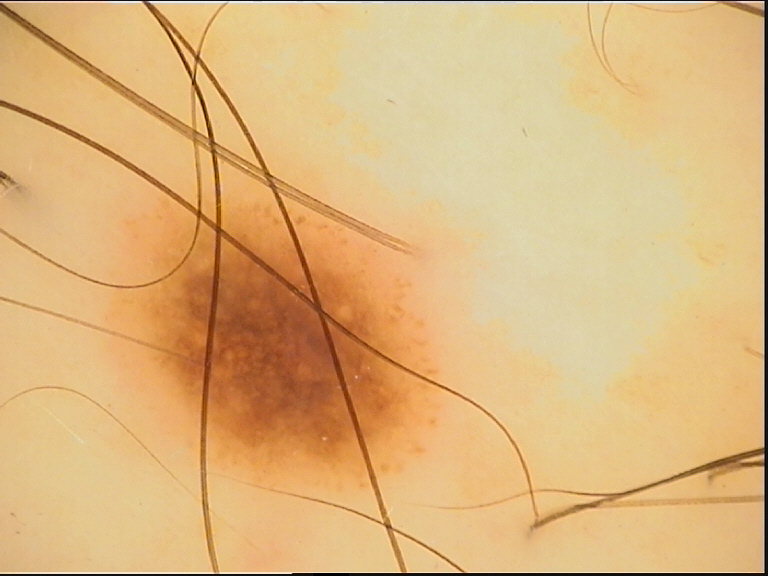Diagnosed as a benign lesion — a dysplastic junctional nevus.